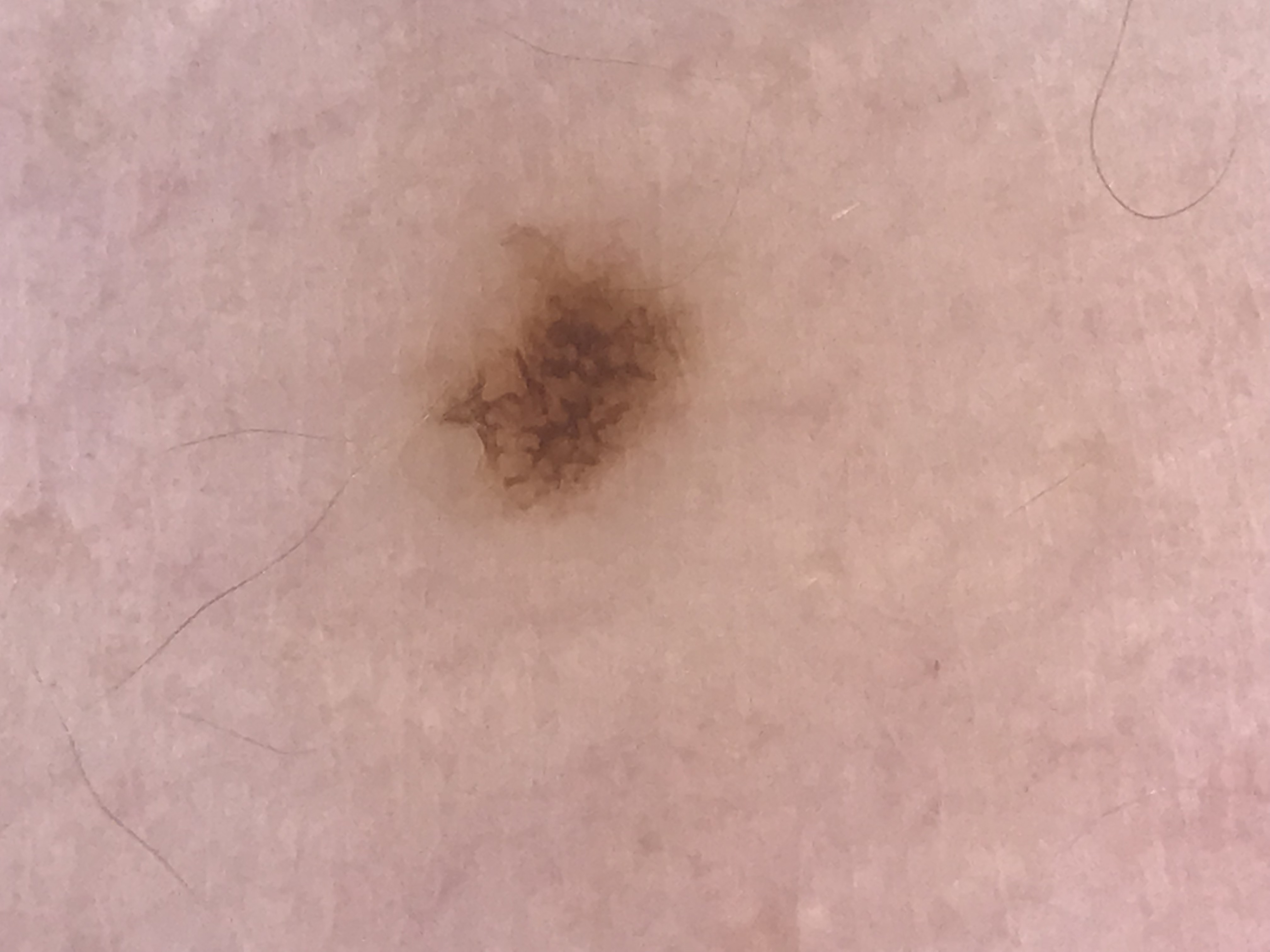<case>
<diagnosis>
<name>dysplastic junctional nevus</name>
<code>jd</code>
<malignancy>benign</malignancy>
<super_class>melanocytic</super_class>
<confirmation>expert consensus</confirmation>
</diagnosis>
</case>